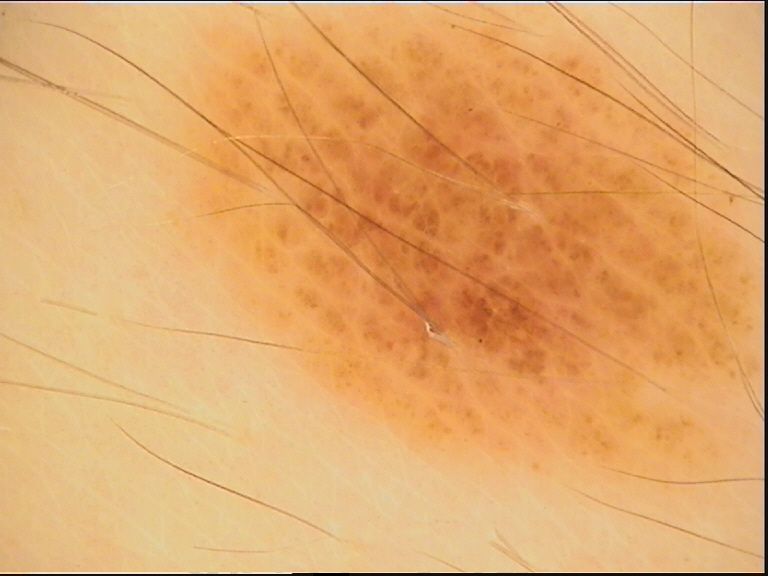A dermoscopic photograph of a skin lesion. The diagnostic label was a compound nevus.